A skin lesion imaged with a dermatoscope: 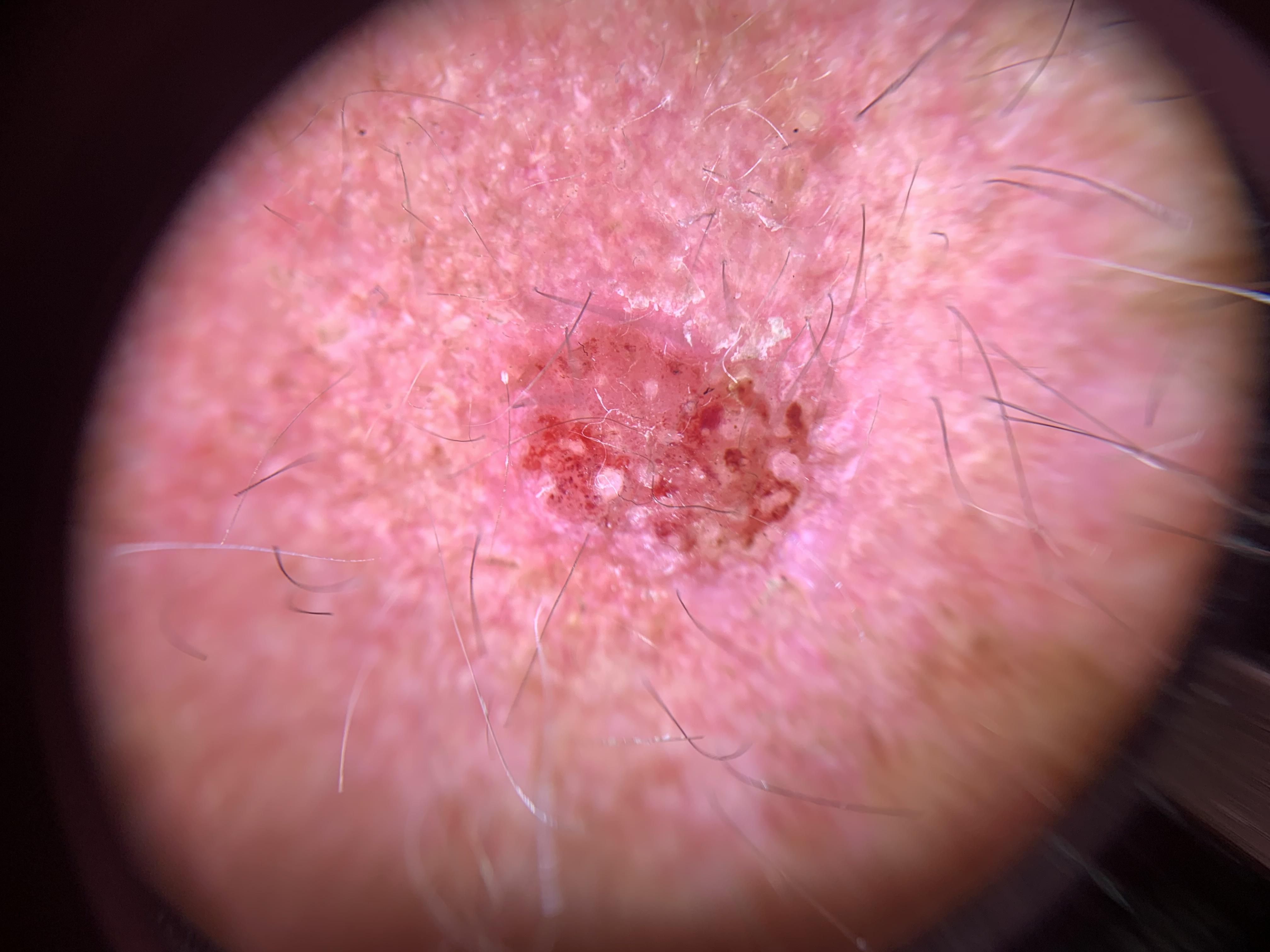| feature | finding |
|---|---|
| body site | the head or neck |
| pathology | Solar or actinic keratosis (biopsy-proven) |